A skin lesion imaged with a dermatoscope.
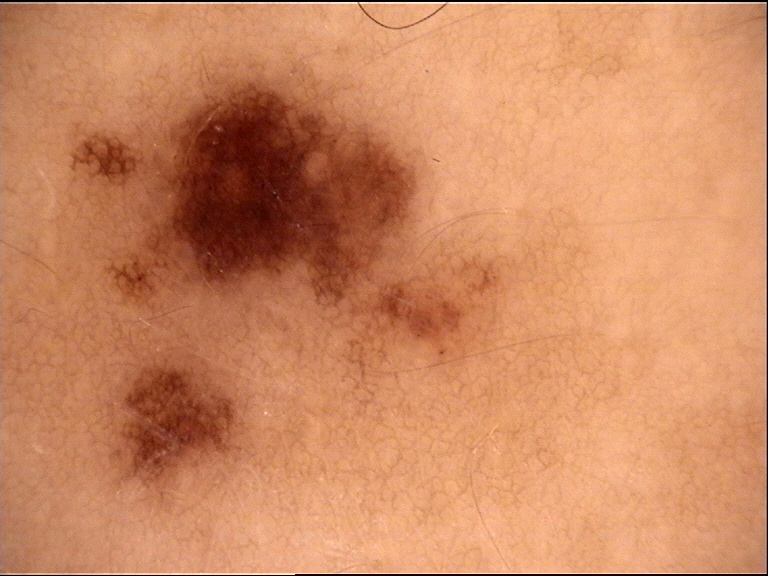Consistent with a dysplastic junctional nevus.